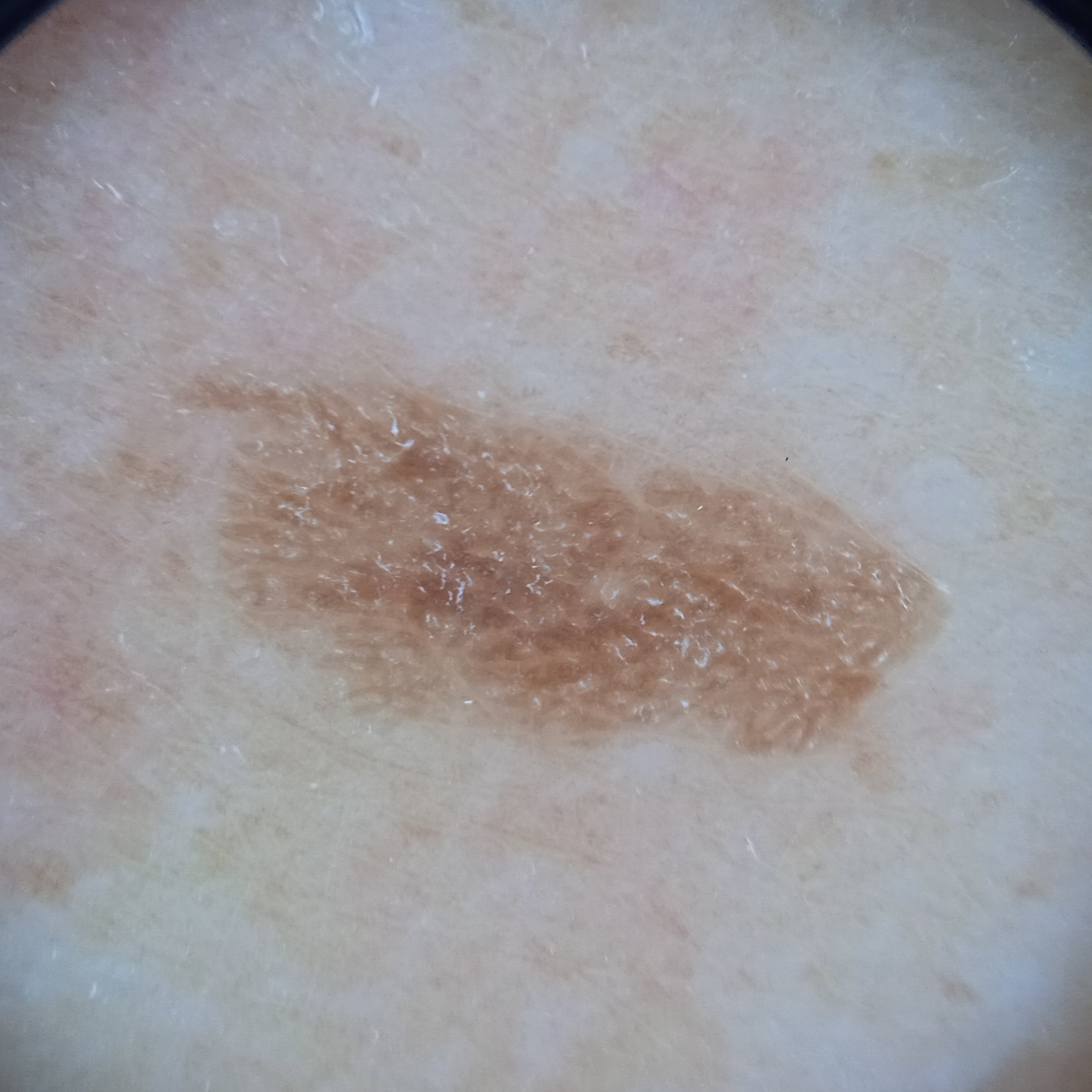The patient says their skin tans without first burning. The patient describes having a moderate number of moles. Acquired for a research image collection, with no referral diagnosis. A female patient 75 years of age. A dermoscopy image of a skin lesion. The patient reports a personal history of skin cancer, a personal history of cancer, and no prior organ transplant. The lesion is on the back. The lesion measures approximately 8.4 mm. The dermatologists' assessment was a seborrheic keratosis.